A close-up photograph · the leg is involved · the patient is 50–59, female · skin tone: Fitzpatrick skin type III; lay reviewers estimated 3 on the Monk Skin Tone · the patient described the issue as a rash · the condition has been present for one to three months · texture is reported as rough or flaky and fluid-filled:
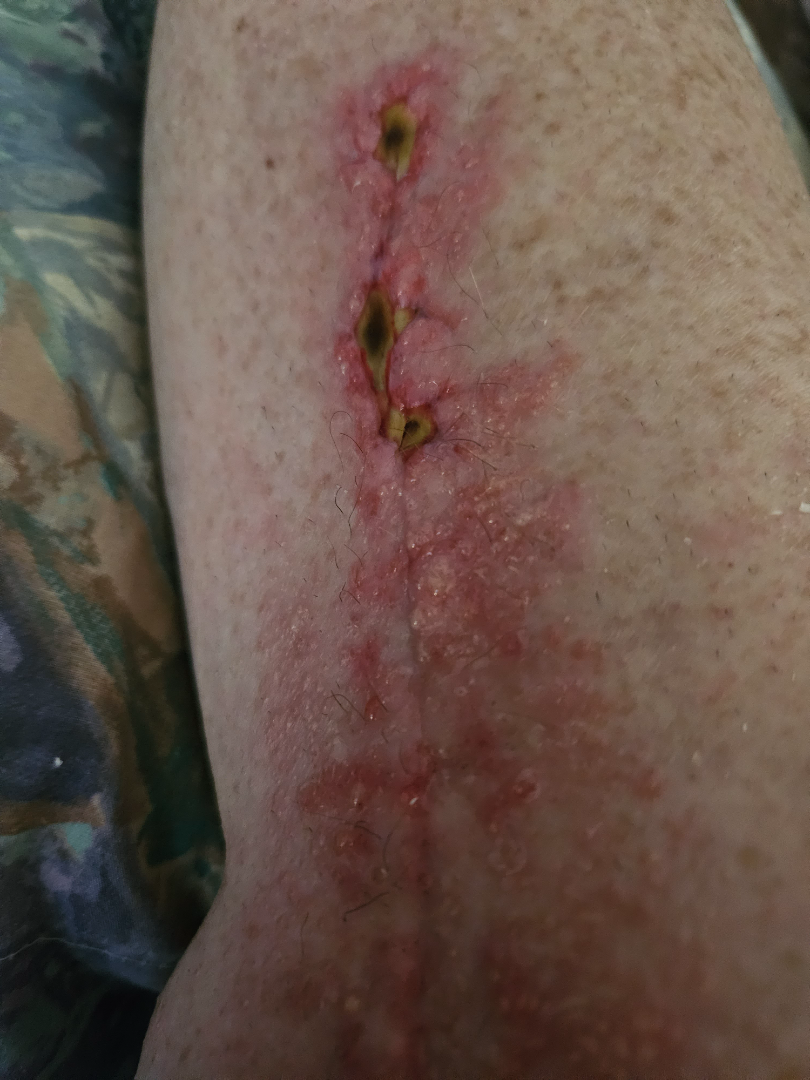assessment=ungradable on photographic review